This image was taken at an angle · the patient is 40–49, female · the condition has been present for one to four weeks · skin tone: self-reported Fitzpatrick skin type III; lay reviewers estimated MST 2 or 4 (two reviewer pools disagreed) · the affected area is the top or side of the foot · the patient considered this a rash.
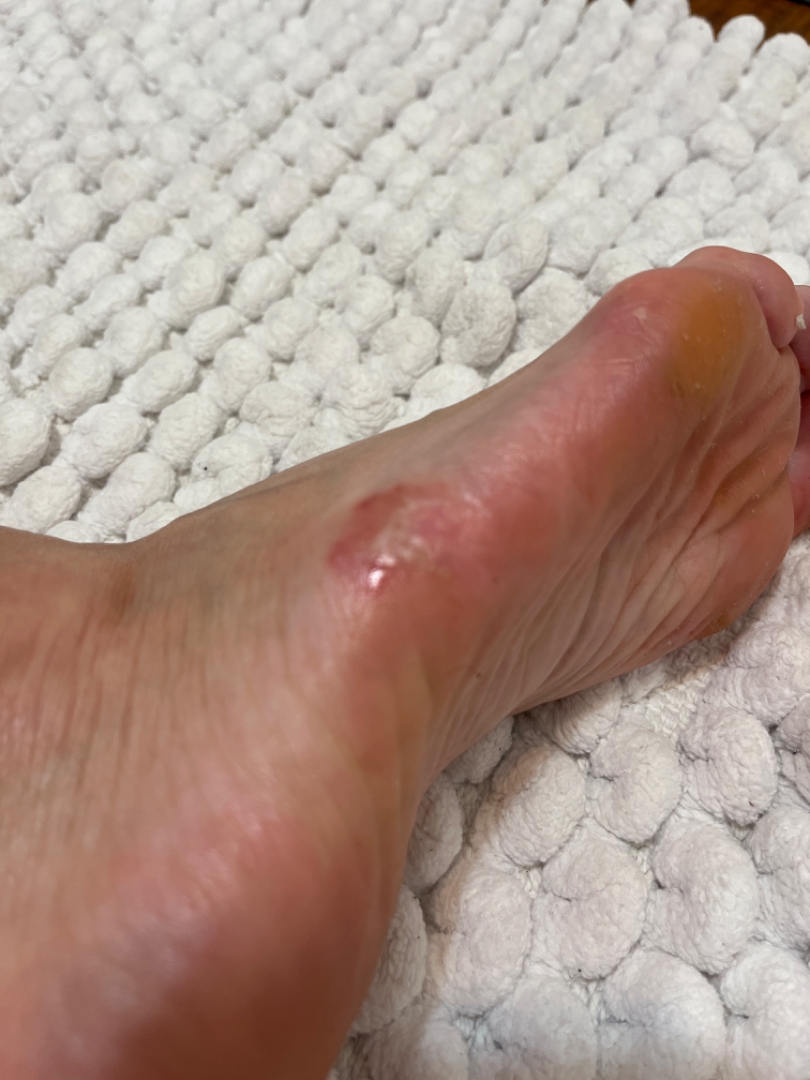The case was difficult to assess from the available photograph.